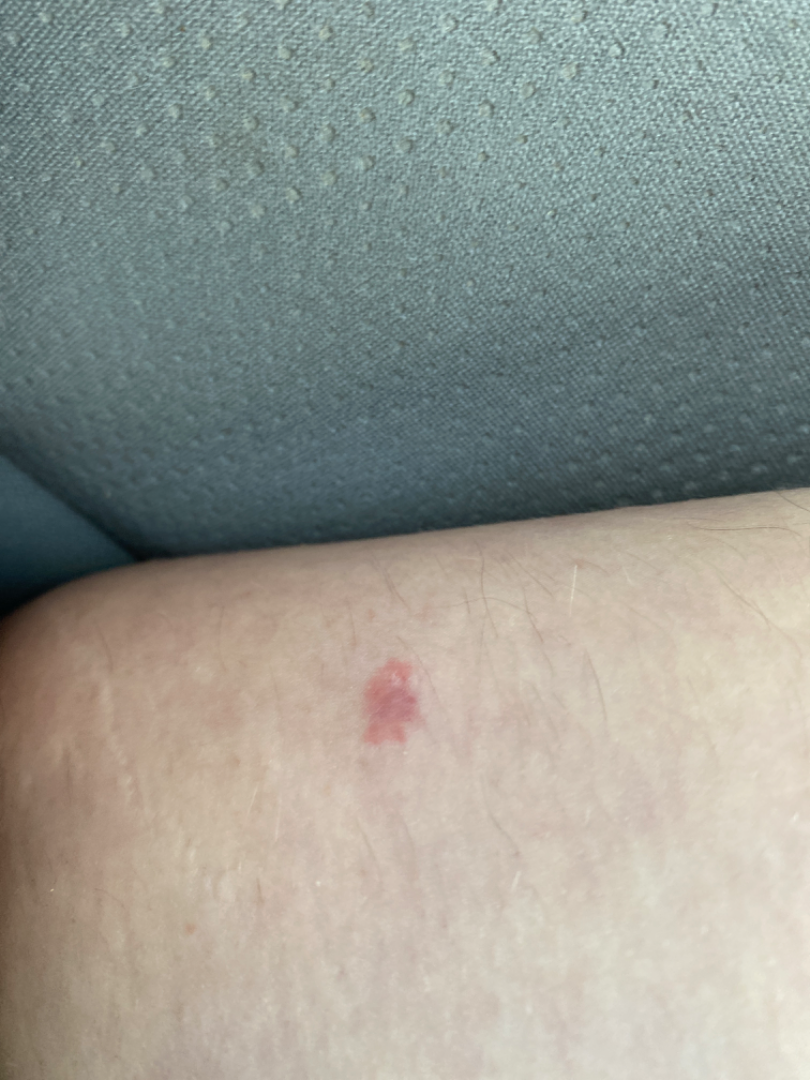Q: What was the assessment?
A: indeterminate
Q: Anatomic location?
A: leg
Q: Texture?
A: rough or flaky
Q: Image view?
A: at a distance
Q: How long has this been present?
A: less than one week
Q: How does the patient describe it?
A: a rash
Q: Any systemic symptoms?
A: none reported